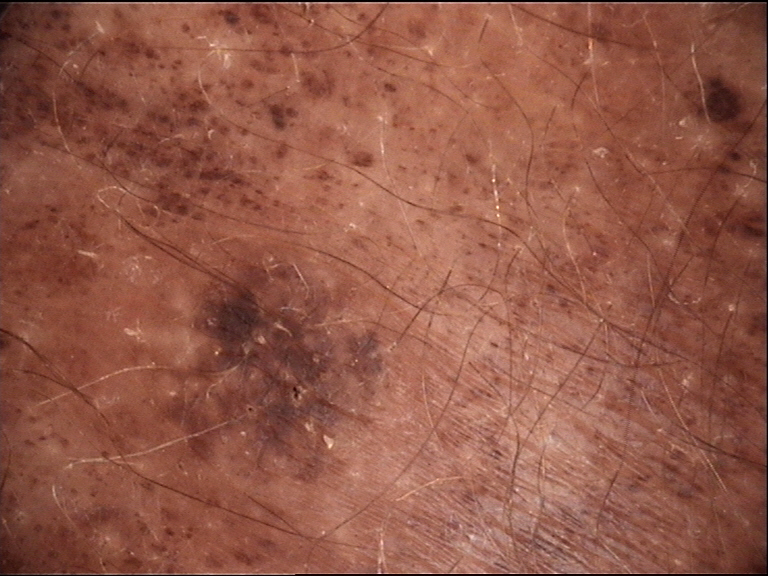imaging=dermoscopy
classification=banal
class=congenital compound nevus (expert consensus)